No constitutional symptoms were reported · the affected area is the head or neck and front of the torso · the lesion is associated with itching · an image taken at a distance · the lesion is described as fluid-filled · the condition has been present for about one day · the patient described the issue as a rash · skin tone: Fitzpatrick skin type II; lay graders estimated a Monk Skin Tone of 2 · the patient is female: 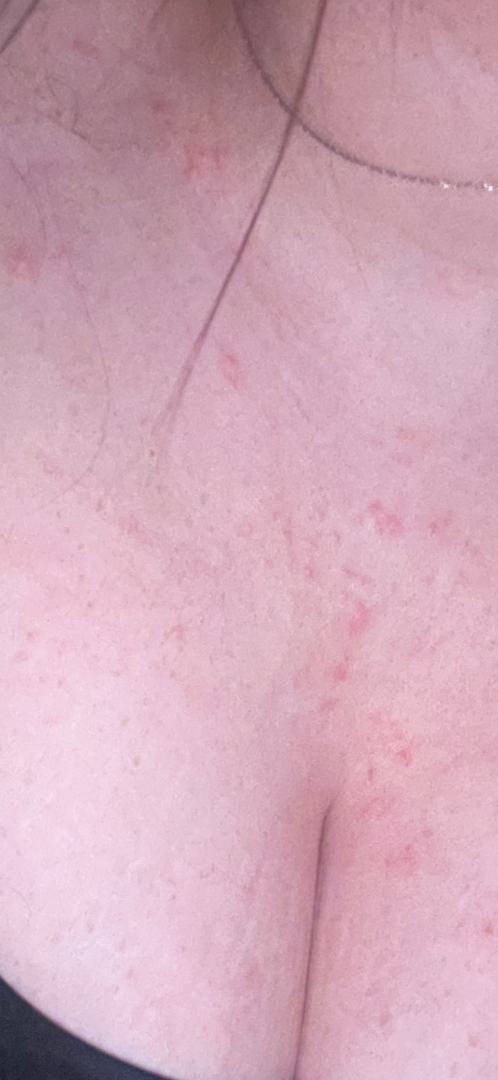Q: What conditions are considered?
A: one reviewing dermatologist: most consistent with Folliculitis; possibly Acne; also on the differential is Eczema